A dermoscopy image of a single skin lesion: 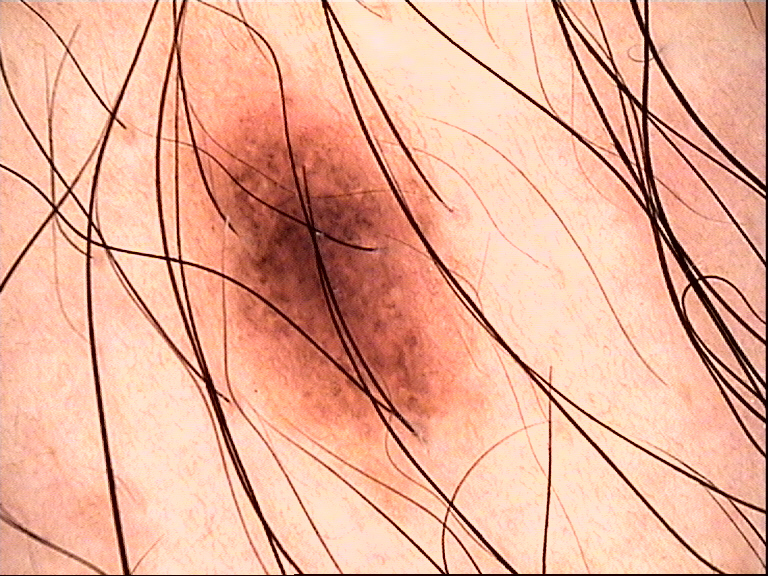  diagnosis:
    name: dysplastic compound nevus
    code: cd
    malignancy: benign
    super_class: melanocytic
    confirmation: expert consensus